The subject is a male roughly 35 years of age; a skin lesion imaged with a dermatoscope:
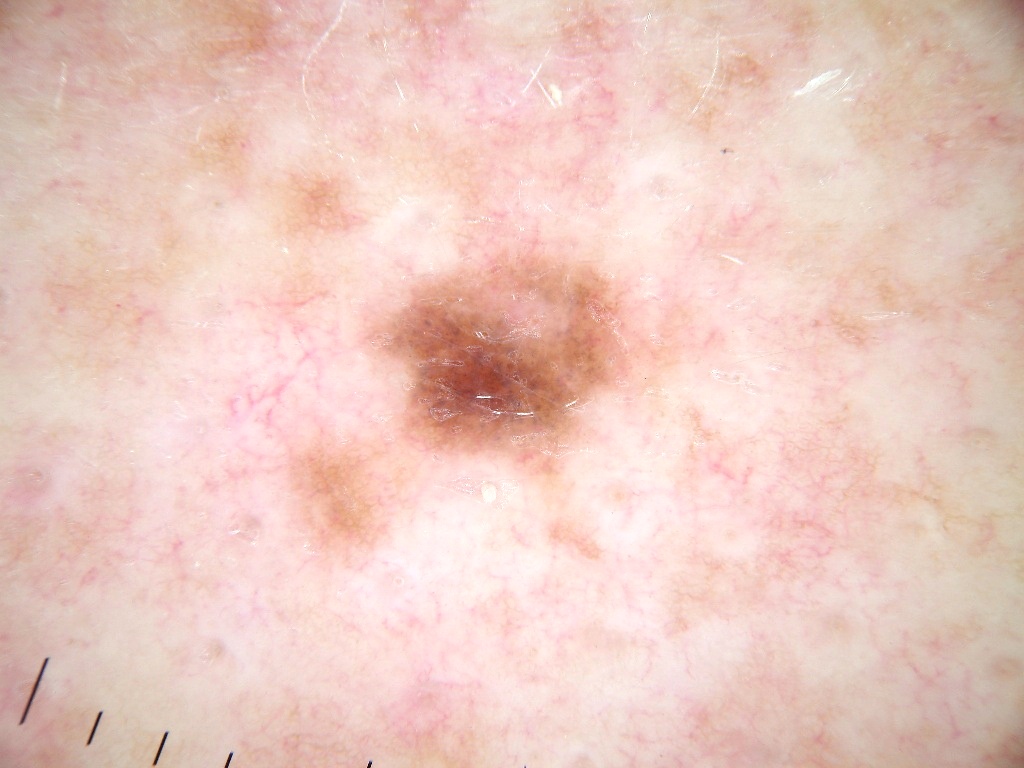<lesion>
<lesion_location>
  <bbox_xyxy>364, 246, 647, 471</bbox_xyxy>
</lesion_location>
<dermoscopic_features>
  <present>pigment network</present>
  <absent>negative network, streaks, globules, milia-like cysts</absent>
</dermoscopic_features>
<diagnosis>
  <name>melanocytic nevus</name>
  <malignancy>benign</malignancy>
  <lineage>melanocytic</lineage>
  <provenance>clinical</provenance>
</diagnosis>
</lesion>